A skin lesion imaged with a dermatoscope.
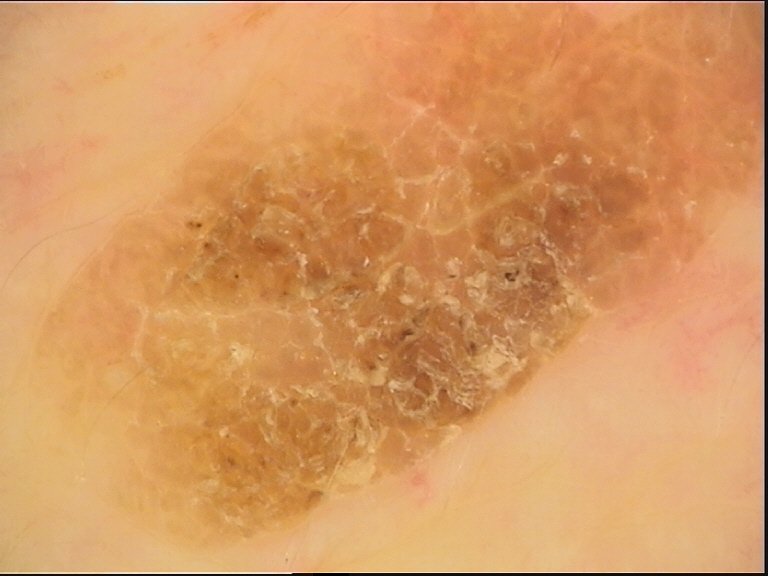| key | value |
|---|---|
| assessment | seborrheic keratosis (expert consensus) |